The contributor is female; located on the top or side of the foot; close-up view: 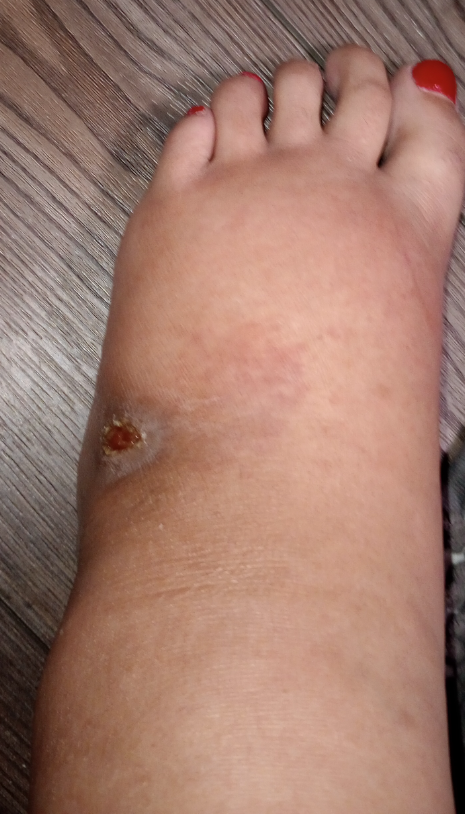The patient indicates the condition has been present for one to three months. Reported lesion symptoms include itching, pain, darkening, enlargement, burning and bothersome appearance. The patient indicates associated joint pain and fever. Texture is reported as fluid-filled. The differential is split between Foot ulcer and Stasis Dermatitis; also consider Leukocytoclastic Vasculitis.